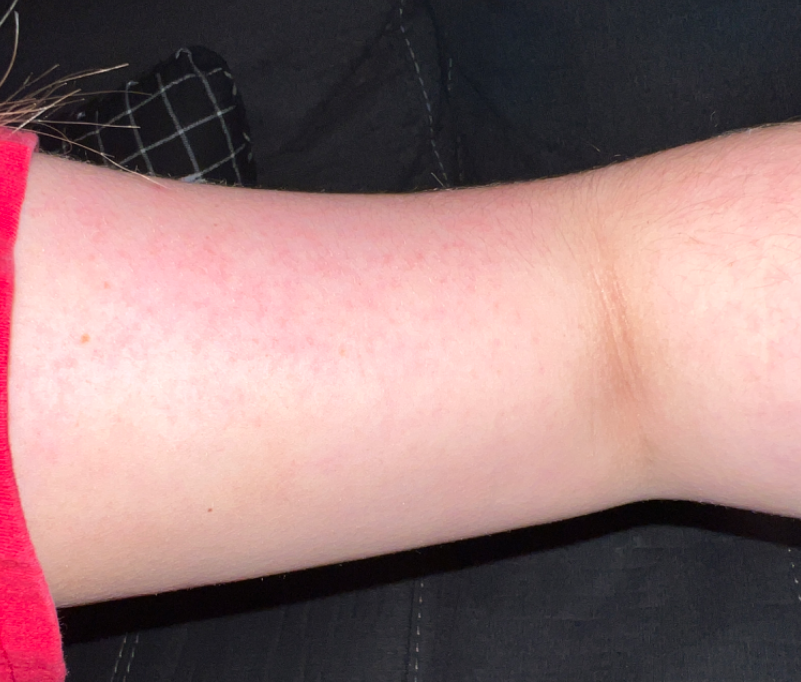assessment: indeterminate.